A dermoscopy image of a single skin lesion:
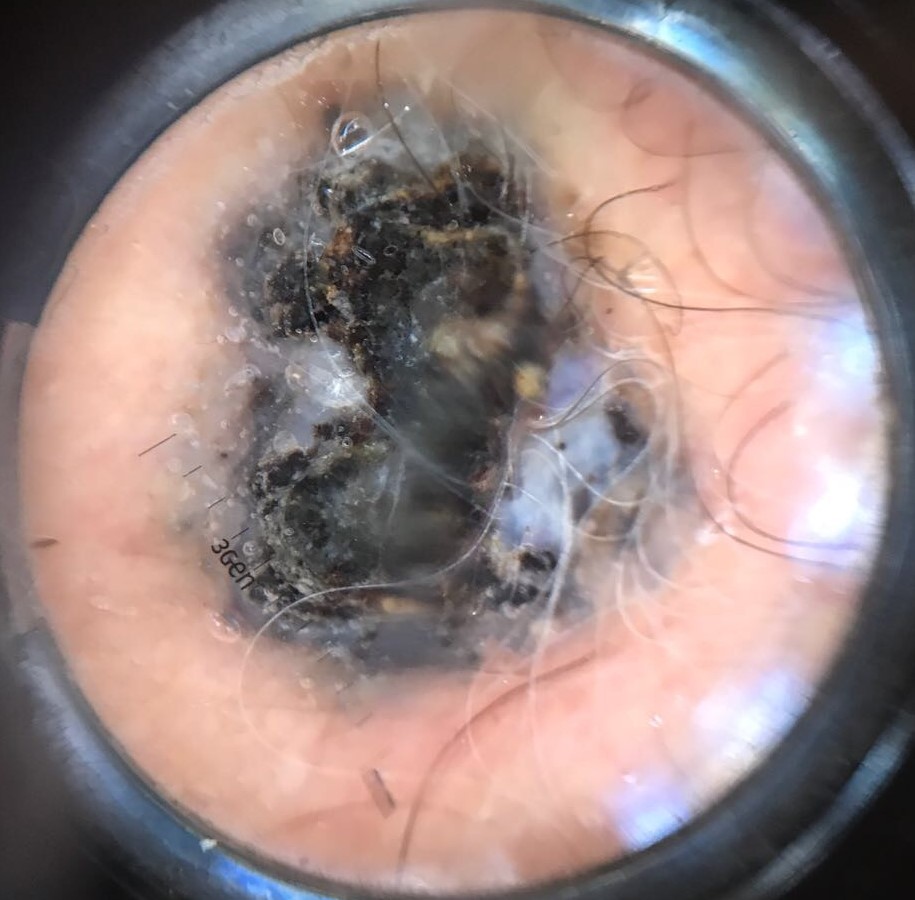| feature | finding |
|---|---|
| diagnostic label | melanoma (biopsy-proven) |